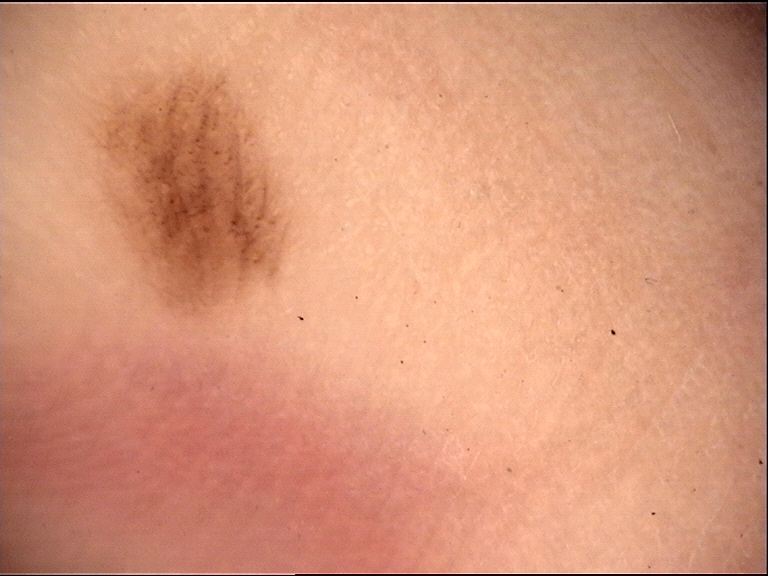Case: A dermoscopic image of a skin lesion. Impression: The diagnosis was an acral dysplastic junctional nevus.